This is a close-up image — 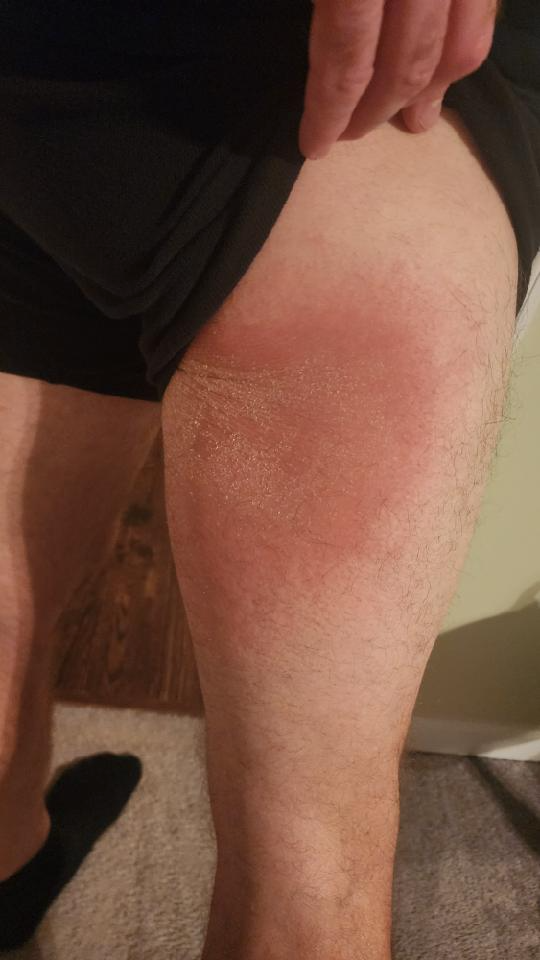Single-reviewer assessment: the leading impression is Cellulitis; also raised was Allergic Contact Dermatitis; less likely is Hypersensitivity.